Dermoscopy of a skin lesion.
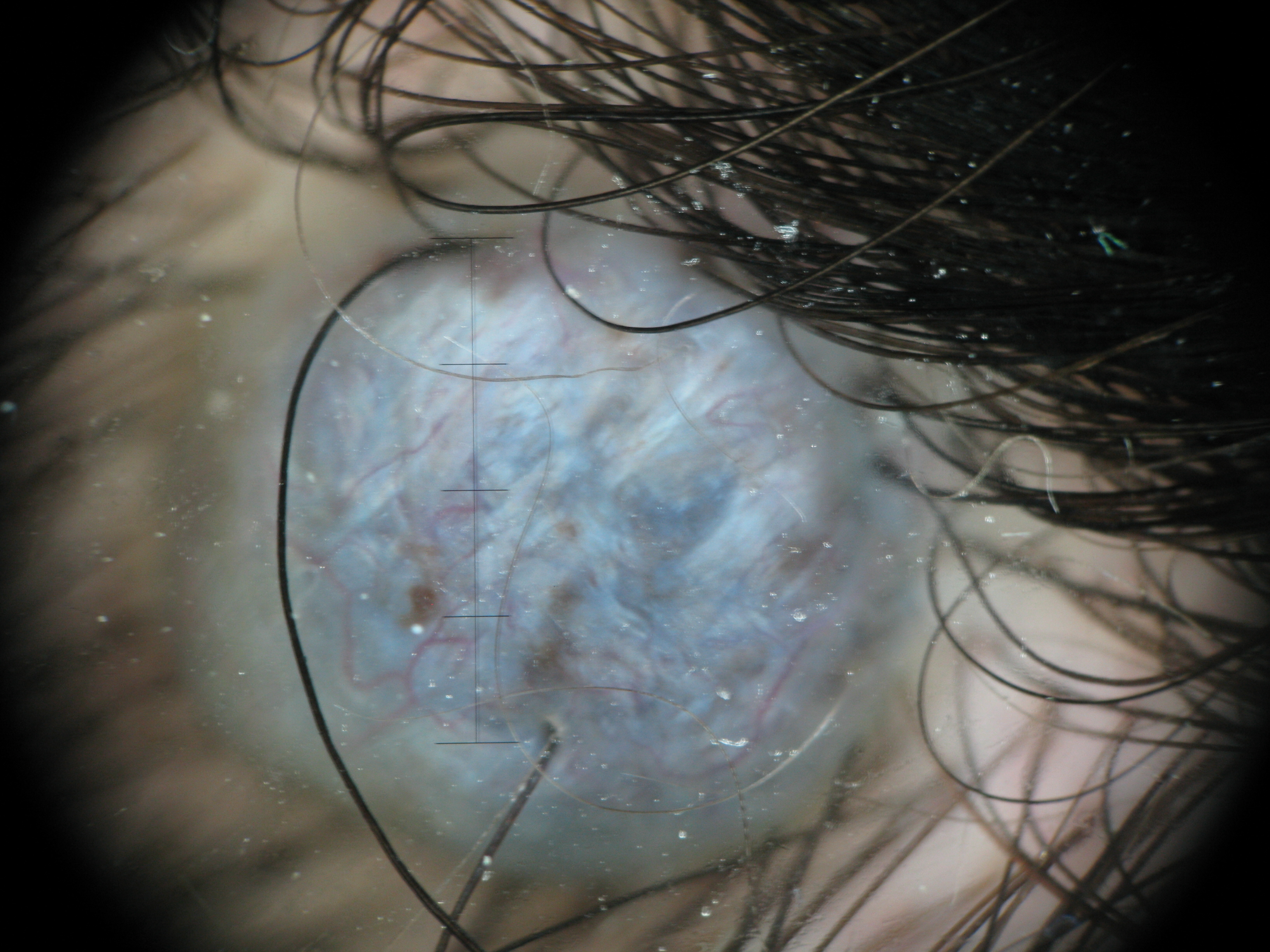The diagnostic label was a banal lesion — a blue nevus.